A skin lesion imaged with a dermatoscope:
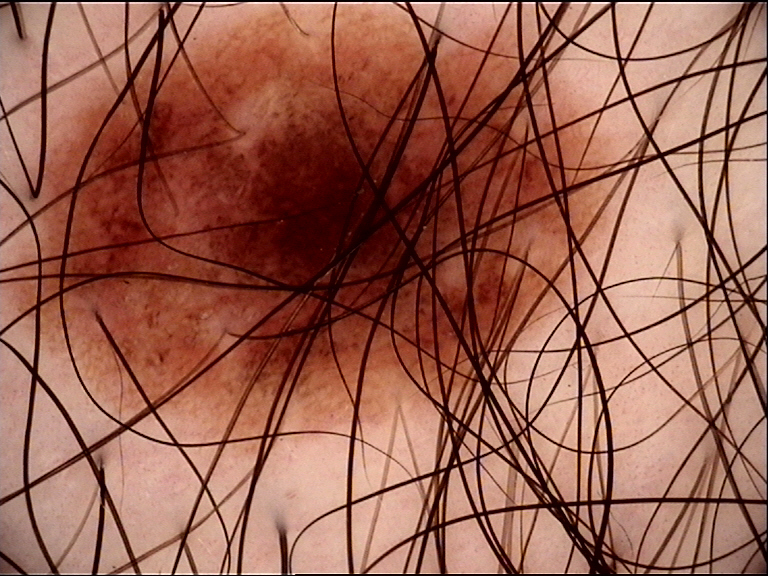The diagnosis was a dysplastic junctional nevus.